Texture is reported as rough or flaky. No relevant systemic symptoms. The patient considered this a rash. The lesion involves the sole of the foot and leg. Self-reported FST III; non-clinician graders estimated Monk Skin Tone 5 (US pool) or 3 (India pool). The photograph was taken at a distance. The contributor is 50–59, female: 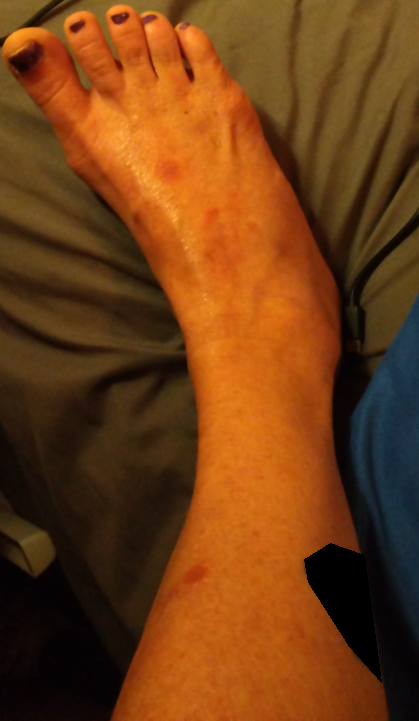Findings: The image was not sufficient for the reviewer to characterize the skin condition.